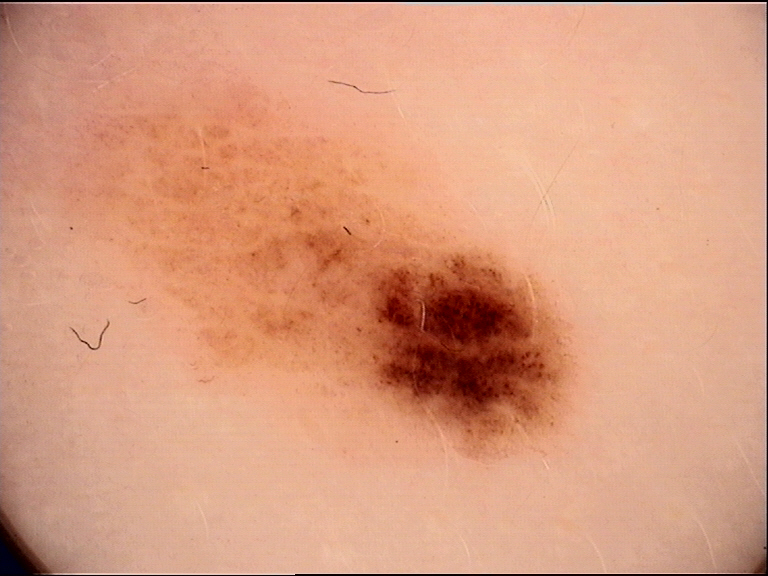• image · dermatoscopy
• label · dysplastic junctional nevus (expert consensus)